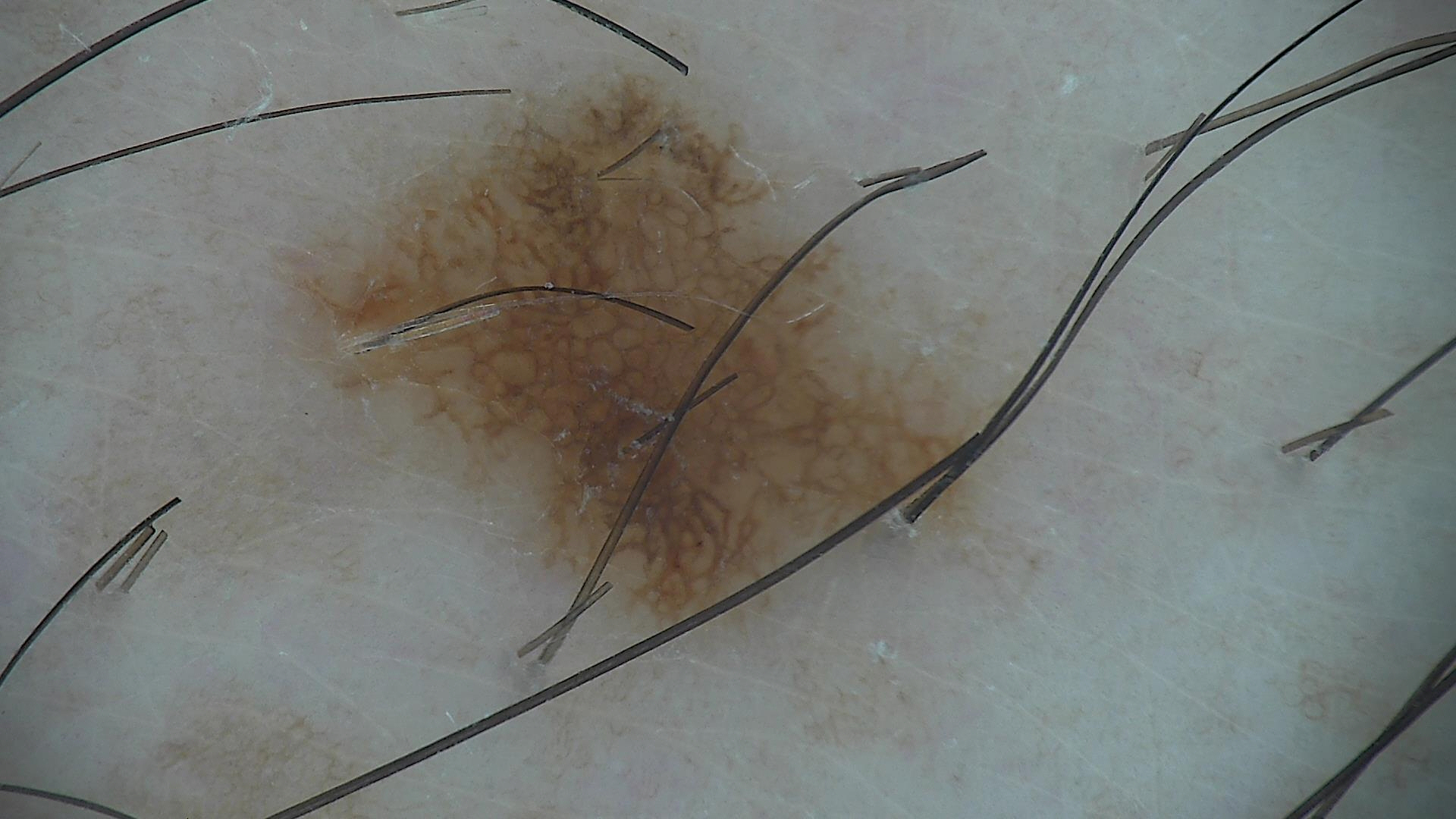A skin lesion imaged with a dermatoscope. Classified as a dysplastic junctional nevus.